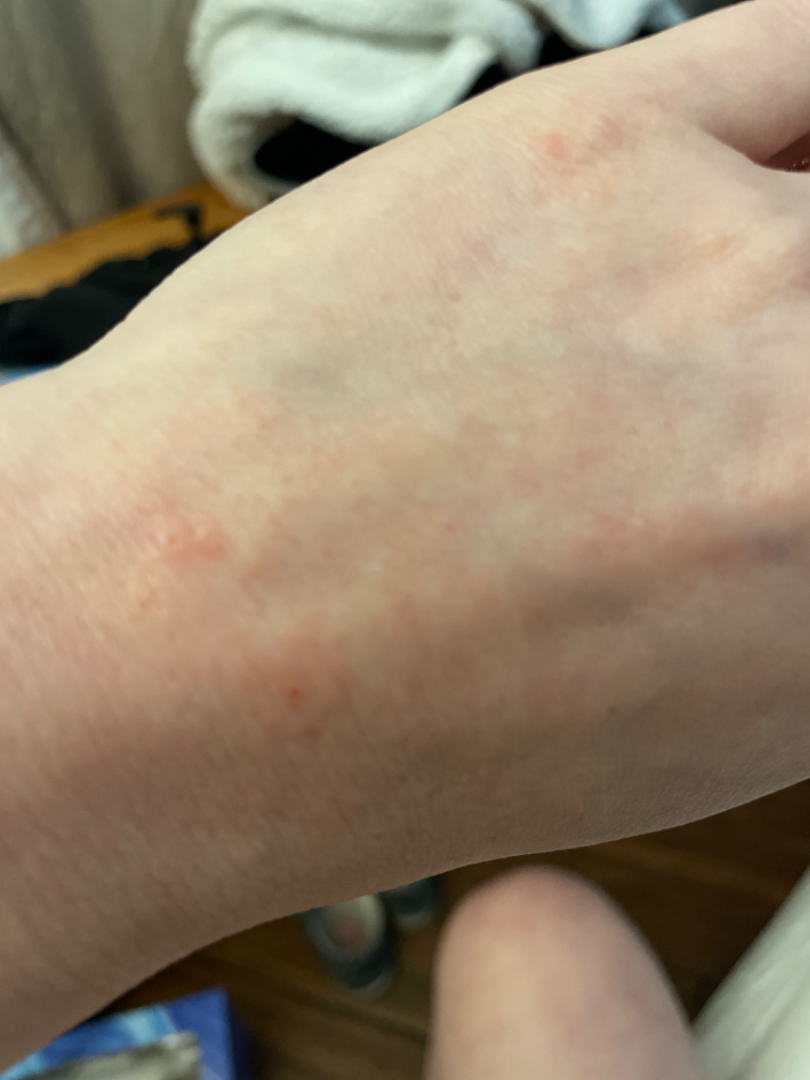impression=most consistent with Insect Bite.